A dermoscopic photograph of a skin lesion.
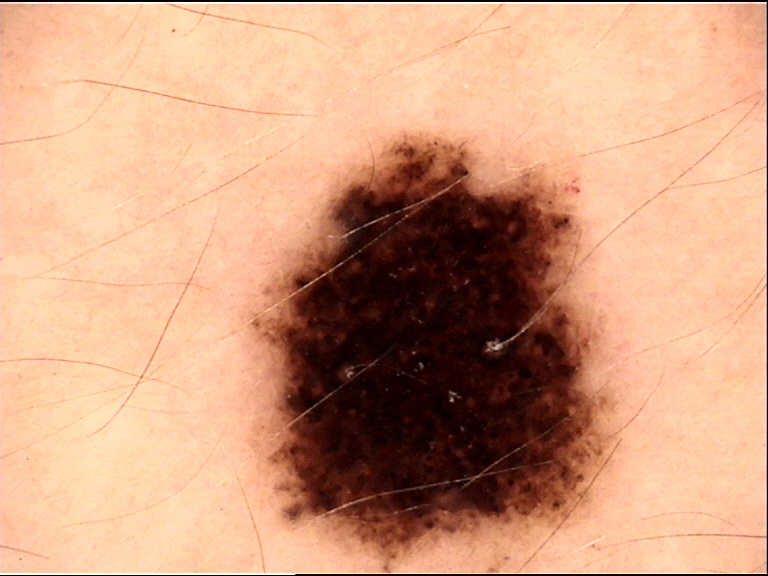Labeled as a dysplastic compound nevus.